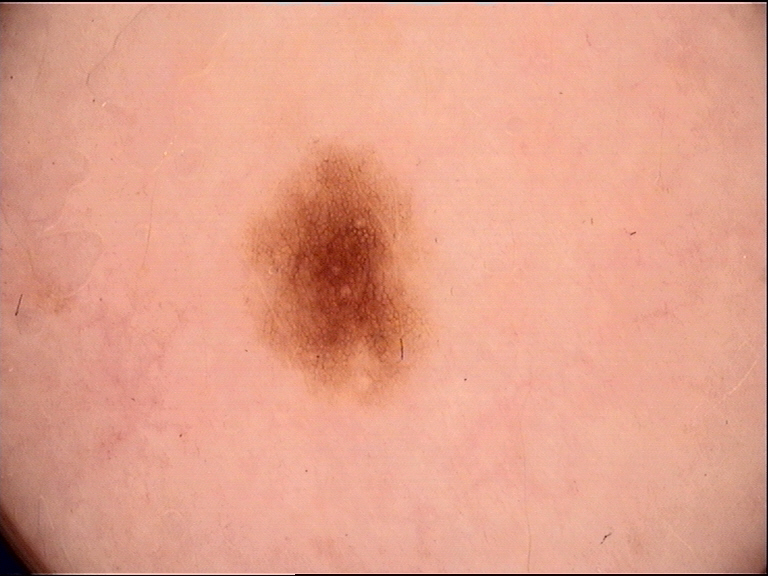Conclusion: The diagnostic label was a benign lesion — a dysplastic junctional nevus.